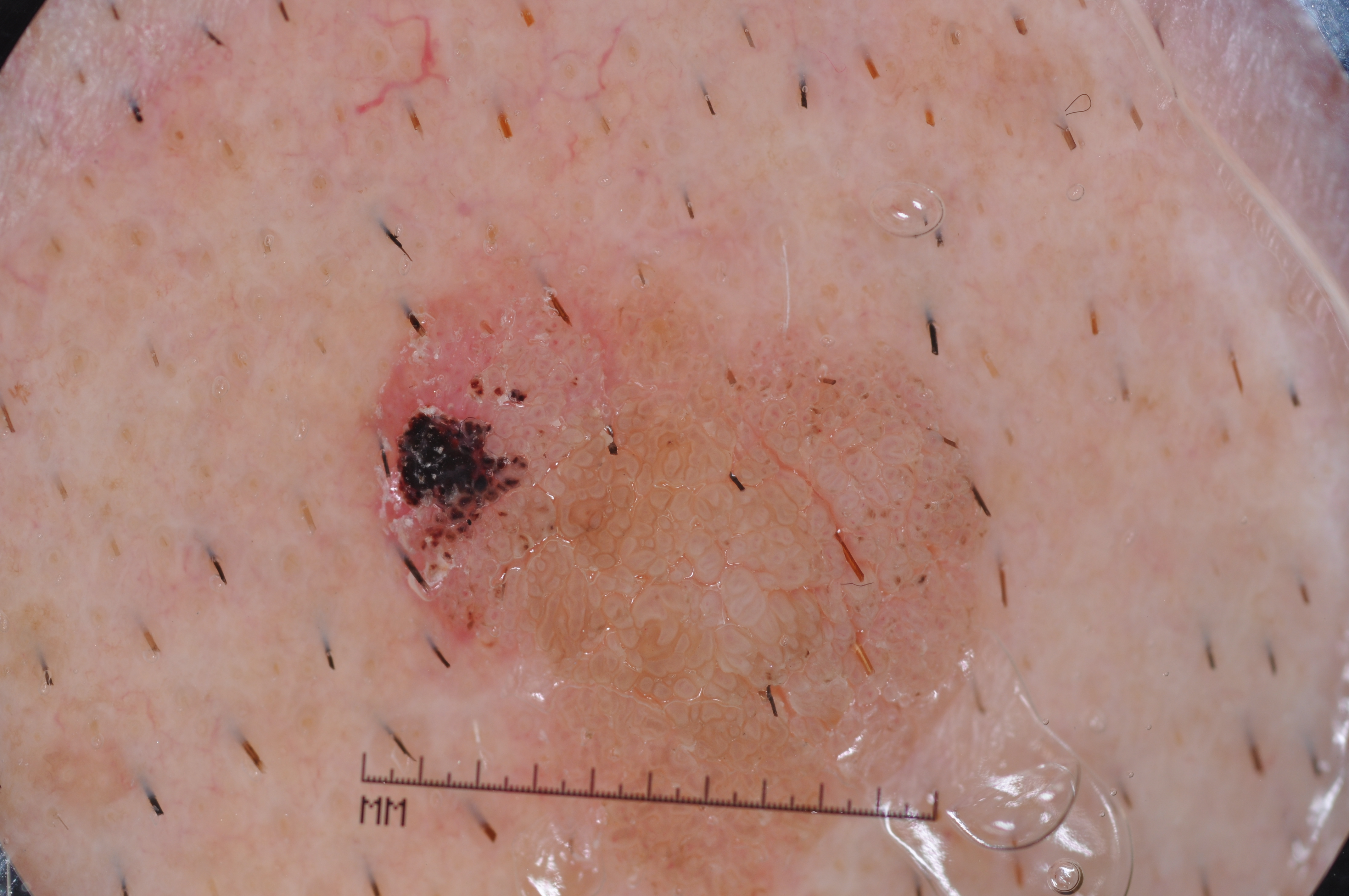| field | value |
|---|---|
| imaging | dermatoscopic image of a skin lesion |
| lesion margin | clipped at the frame edge |
| size | ~24% of the field |
| lesion location | box(348, 259, 1012, 895) |
| dermoscopic features assessed but absent | pigment network, streaks, negative network, and milia-like cysts |
| diagnostic label | a seborrheic keratosis, a benign lesion |